A female patient aged around 35. The patient was assessed as Fitzpatrick II. A dermoscopy image of a single skin lesion — 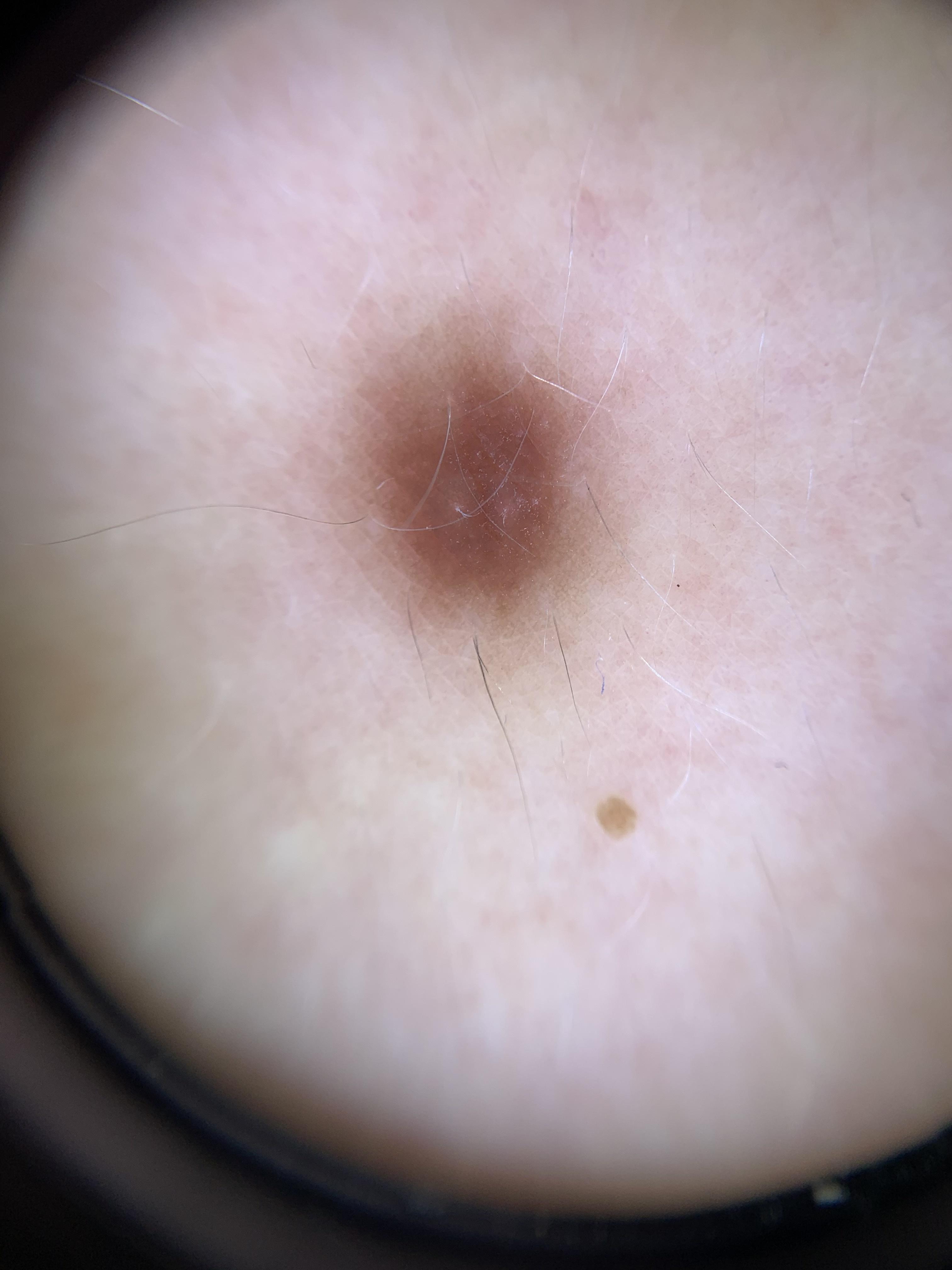anatomic site = the trunk, diagnosis = Dermatofibroma (clinical impression).